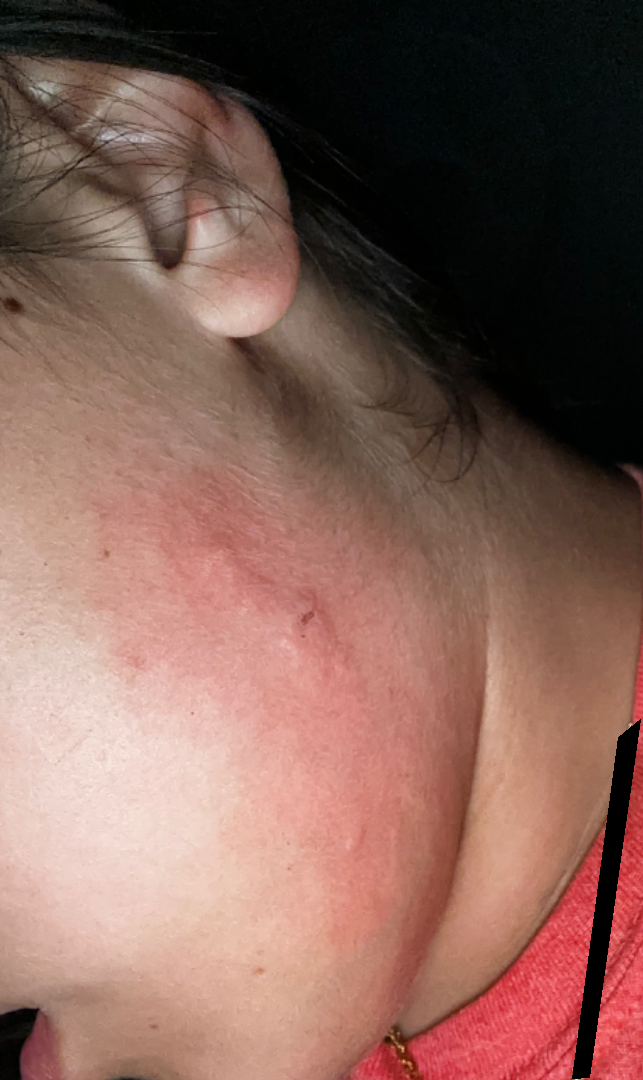<case>
<differential>Scar Condition</differential>
</case>